A dermoscopic close-up of a skin lesion.
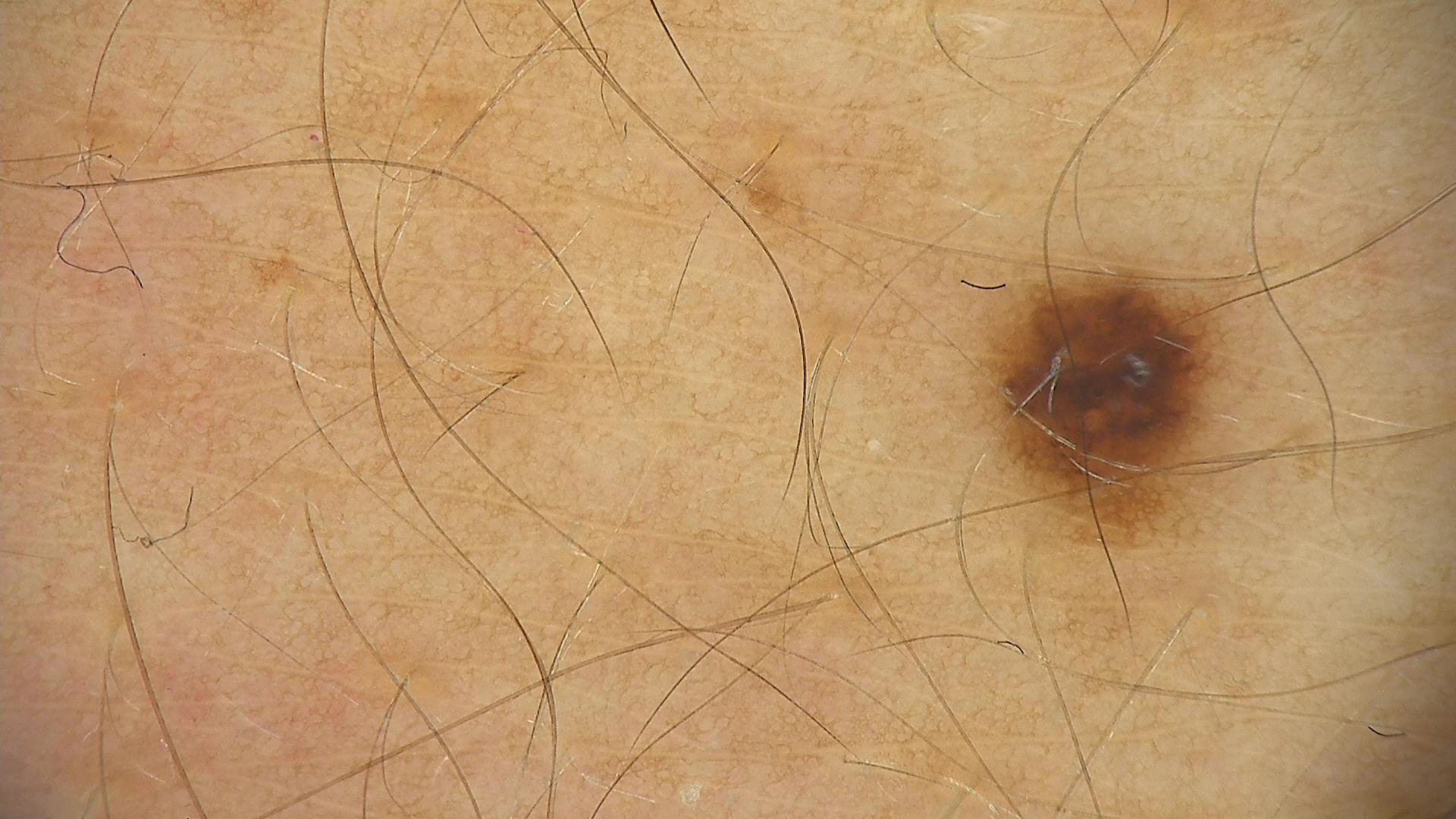Q: What was the diagnostic impression?
A: dysplastic junctional nevus (expert consensus)